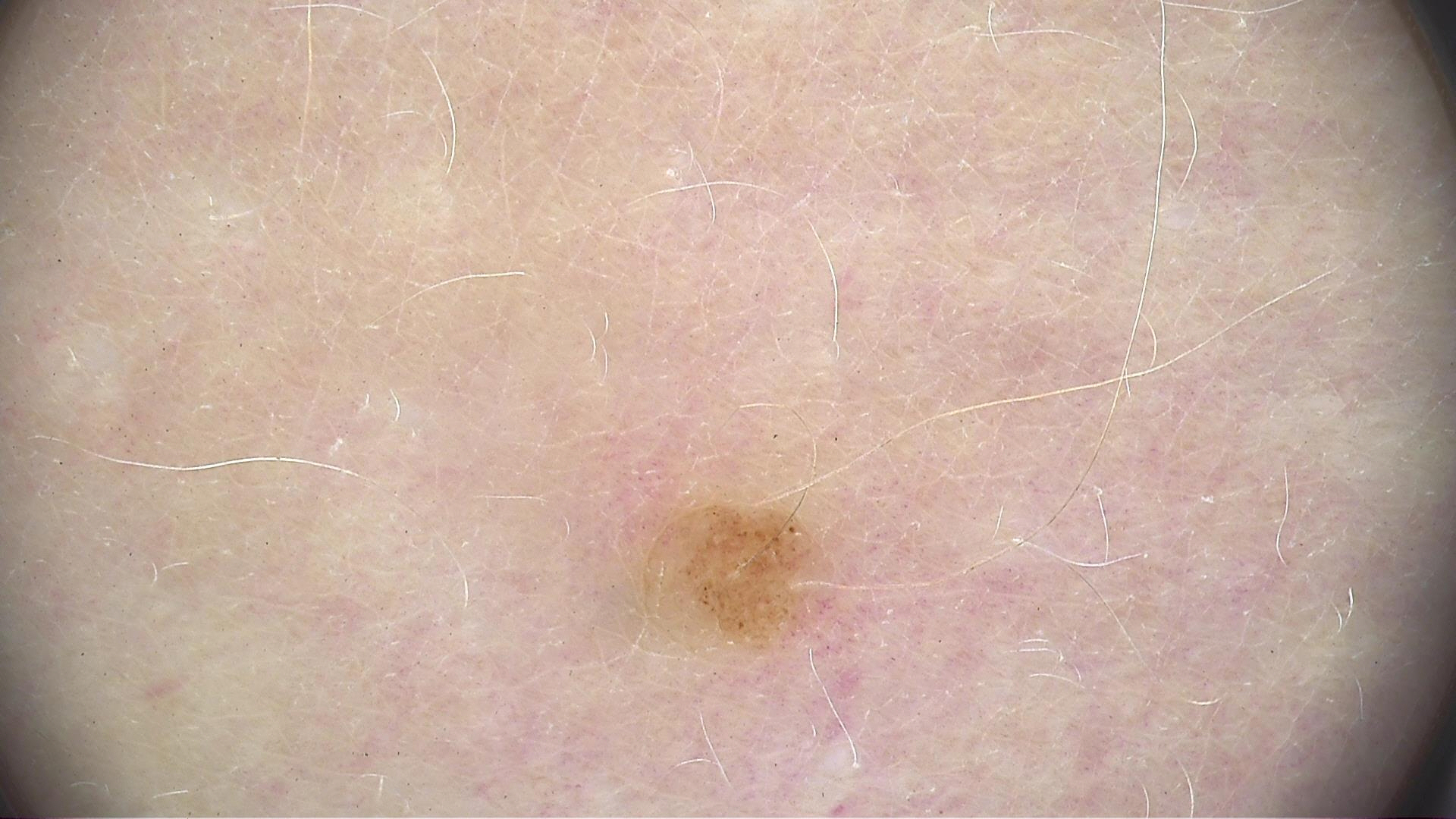classification: banal, diagnostic label: dermal nevus (expert consensus).